Close-up view:
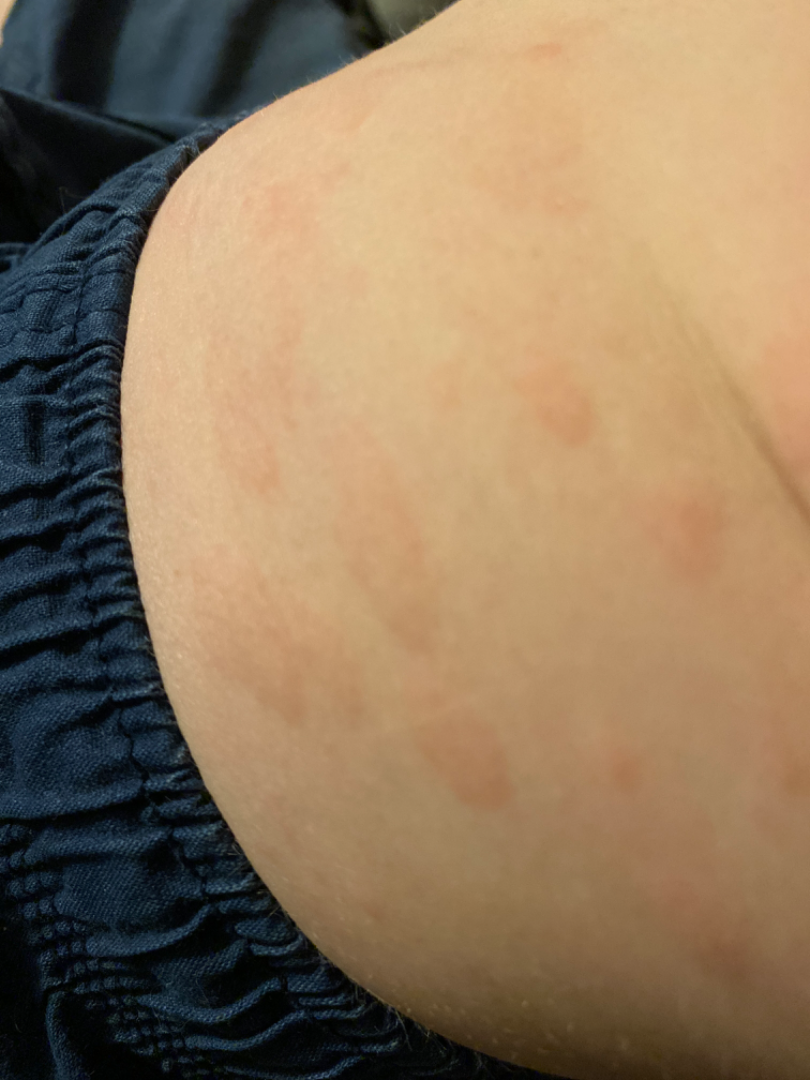Reviewed remotely by one dermatologist: in keeping with Urticaria.